A dermoscopic image of a skin lesion.
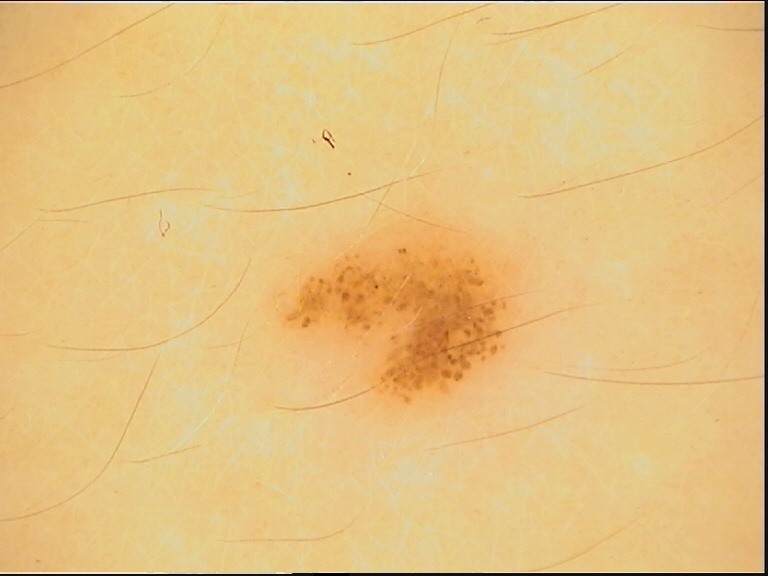Case:
- label · dysplastic junctional nevus (expert consensus)